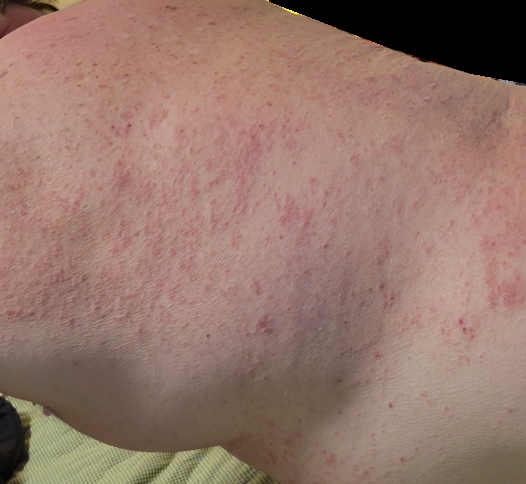Eczema (most likely); Scabies (considered); Allergic Contact Dermatitis (considered).